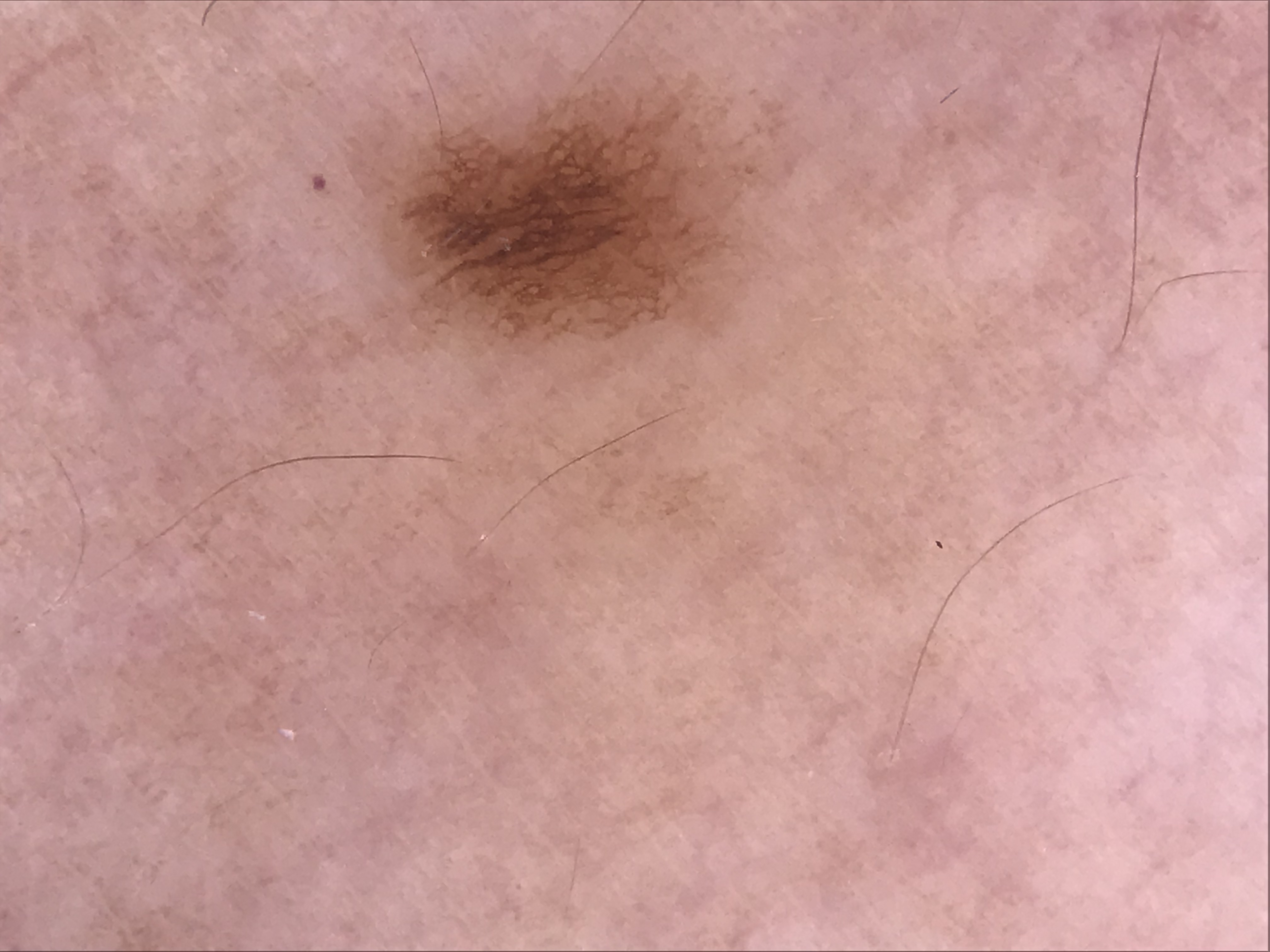A skin lesion imaged with a dermatoscope. Diagnosed as a dysplastic junctional nevus.